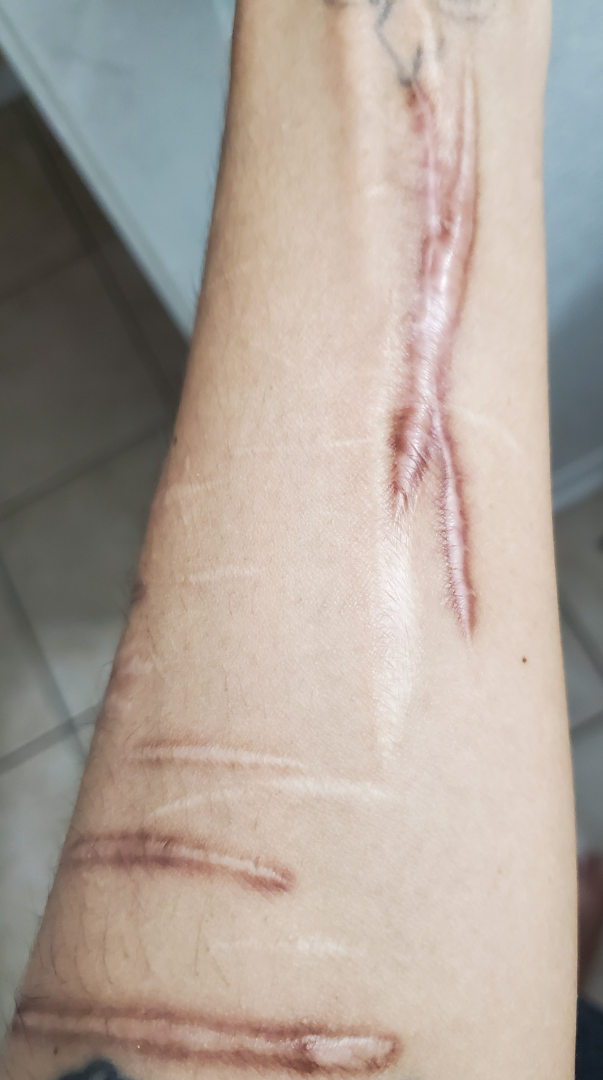The patient reported no systemic symptoms. This image was taken at an angle. The lesion involves the arm. Skin tone: non-clinician graders estimated Monk skin tone scale 3 or 4. Three dermatologists each reviewed the case: the impression is Scar Condition.